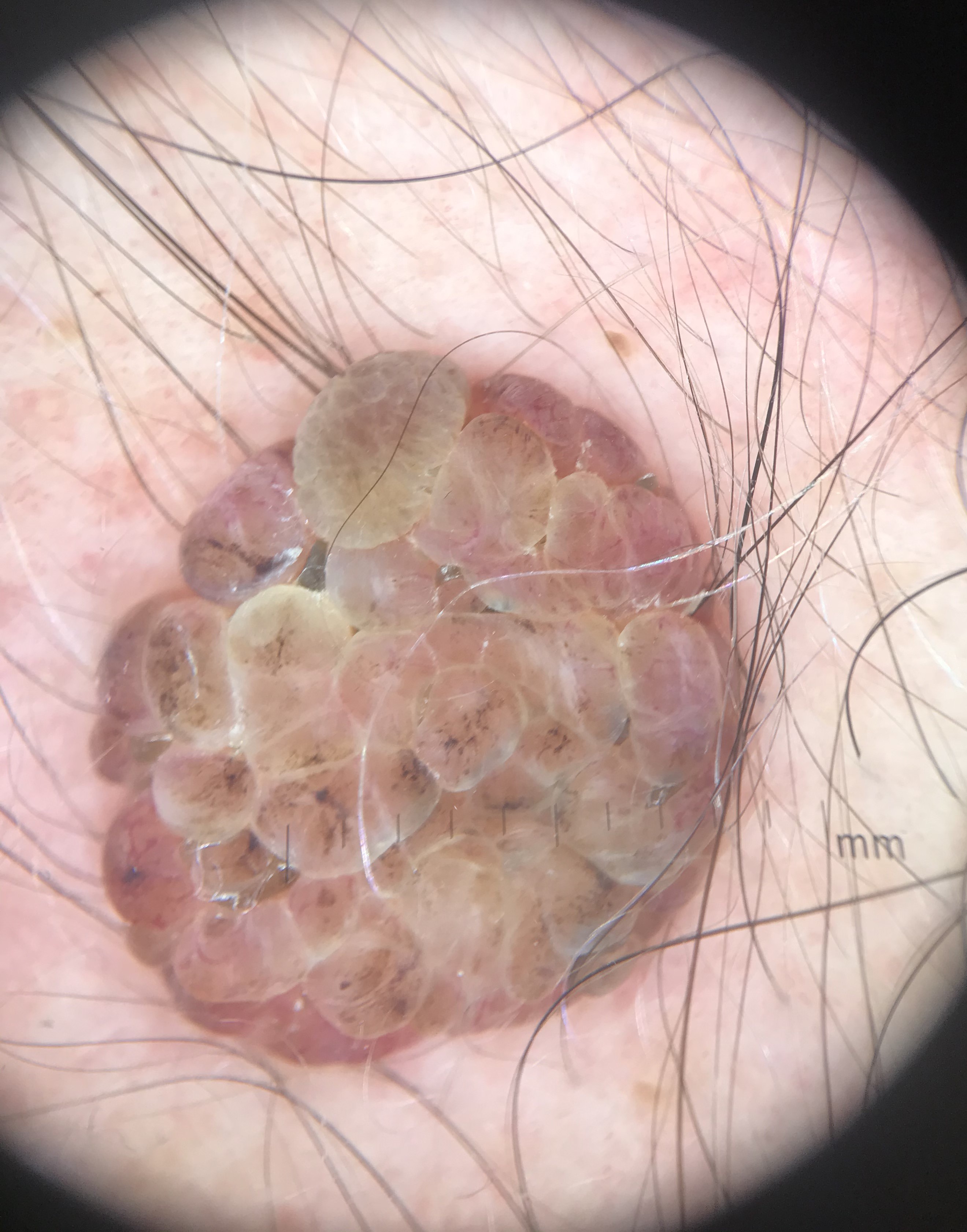class: dermal nevus (expert consensus).